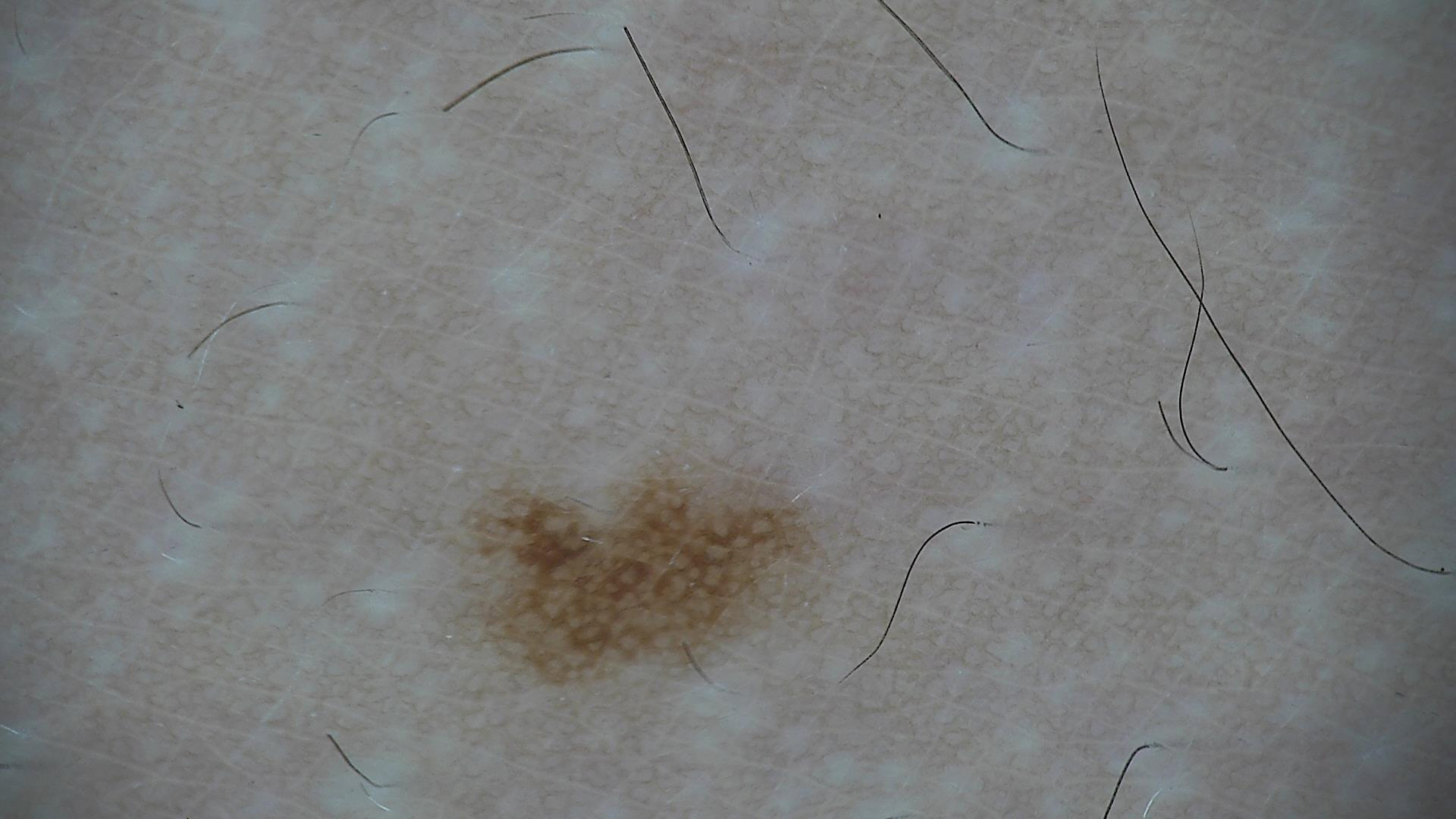Labeled as a benign lesion — a dysplastic junctional nevus.